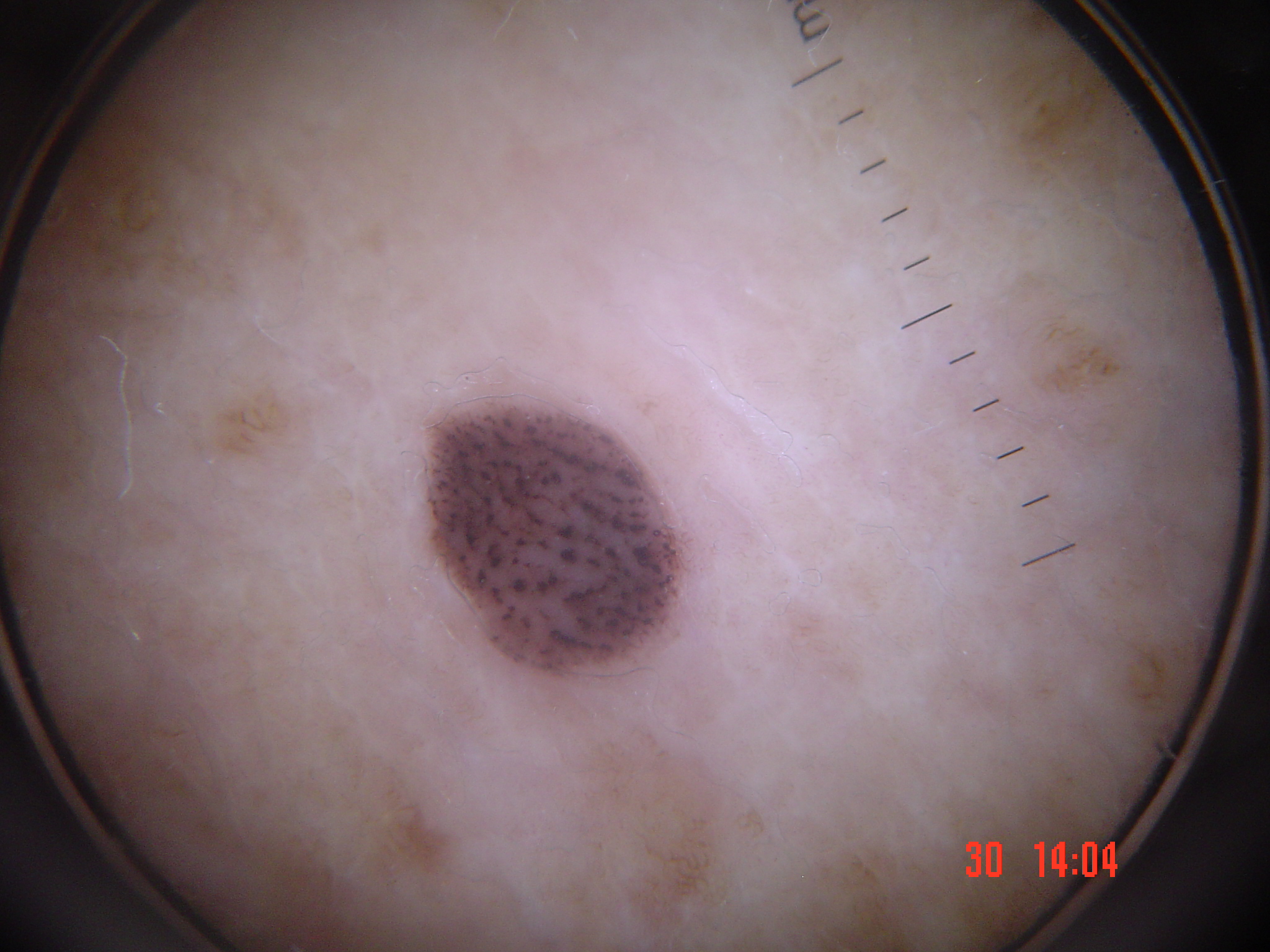Q: What is this lesion?
A: seborrheic keratosis (expert consensus)